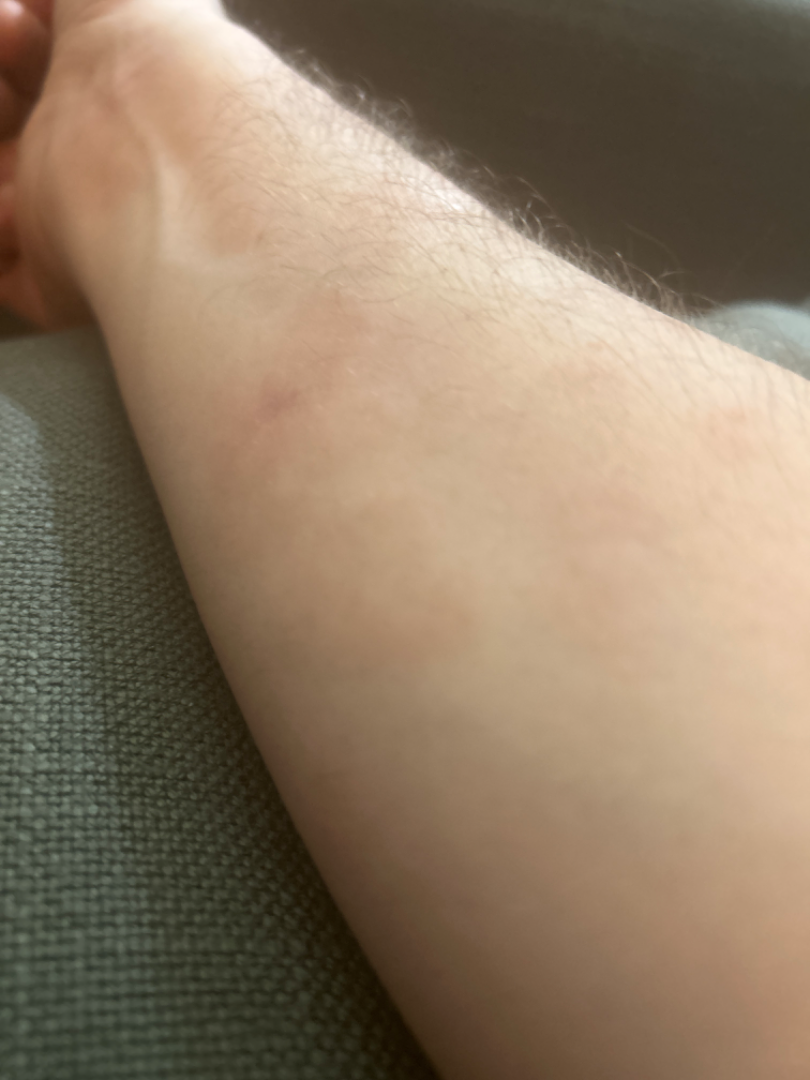duration = one to four weeks; contributor = male, age 40–49; associated systemic symptoms = none reported; shot type = at an angle; reported symptoms = none reported; anatomic site = head or neck, front of the torso, back of the torso, back of the hand and arm; skin tone = Fitzpatrick skin type II.